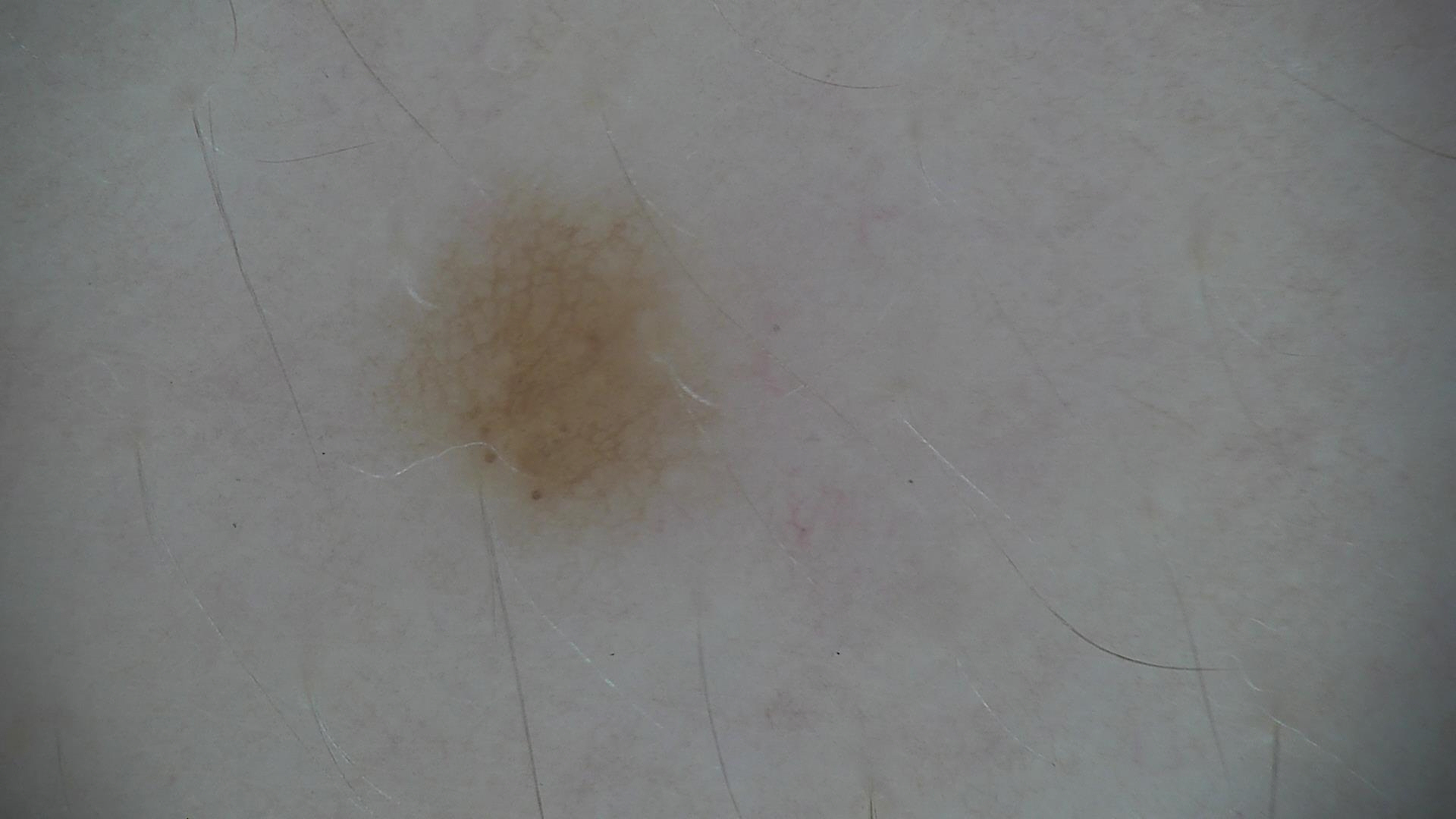image type = dermoscopy, label = dysplastic junctional nevus (expert consensus).